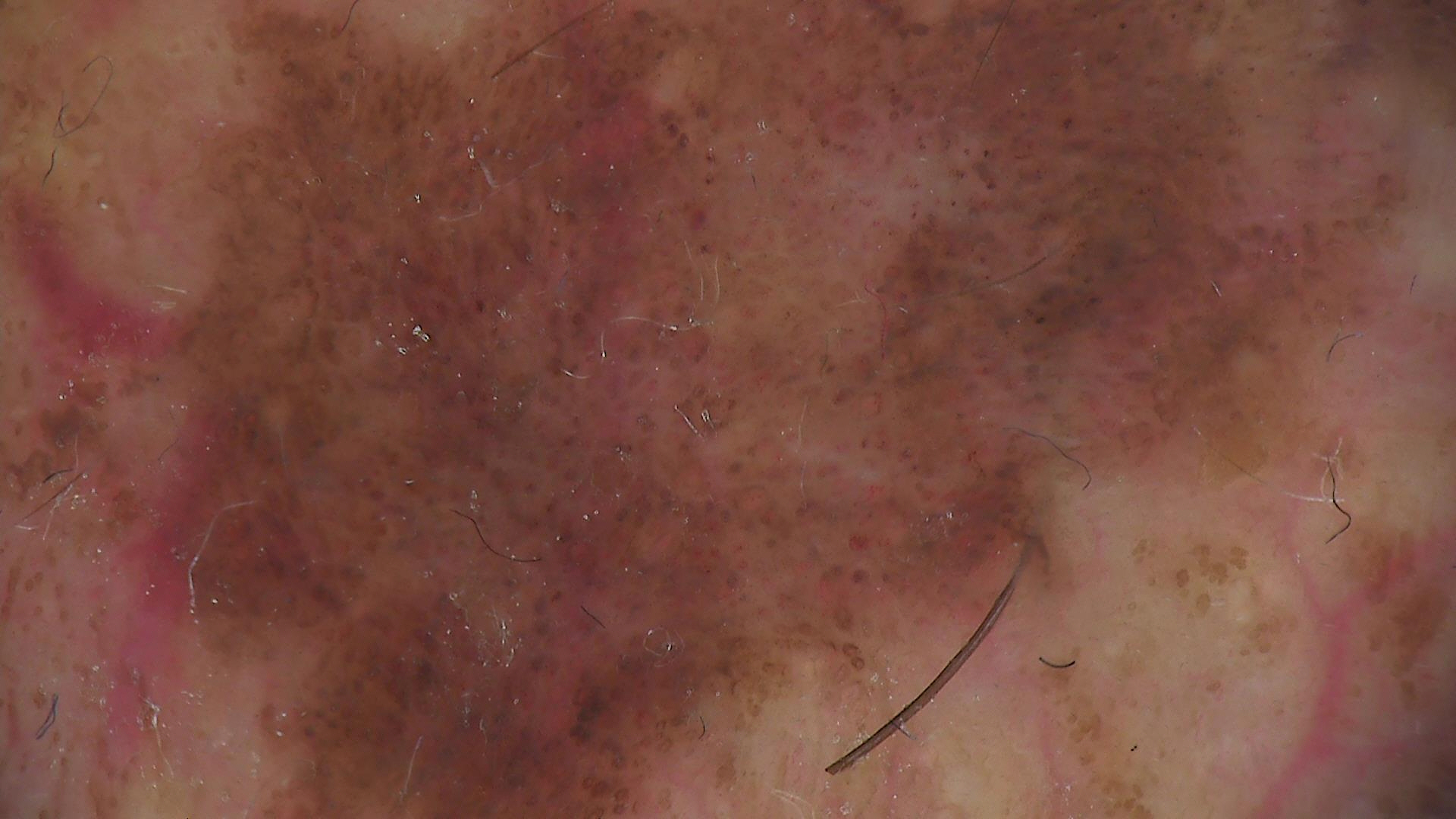A dermoscopic photograph of a skin lesion.
Labeled as a dysplastic compound nevus.